A skin lesion imaged with a dermatoscope.
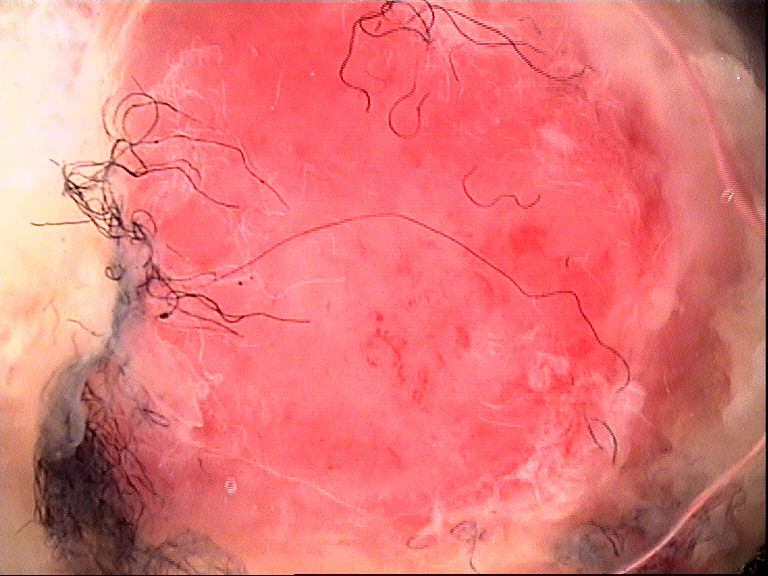Conclusion:
Histopathologically confirmed as a malignancy — an acral nodular melanoma.